The lesion involves the leg; the photograph is a close-up of the affected area; the patient is a male aged 60–69: 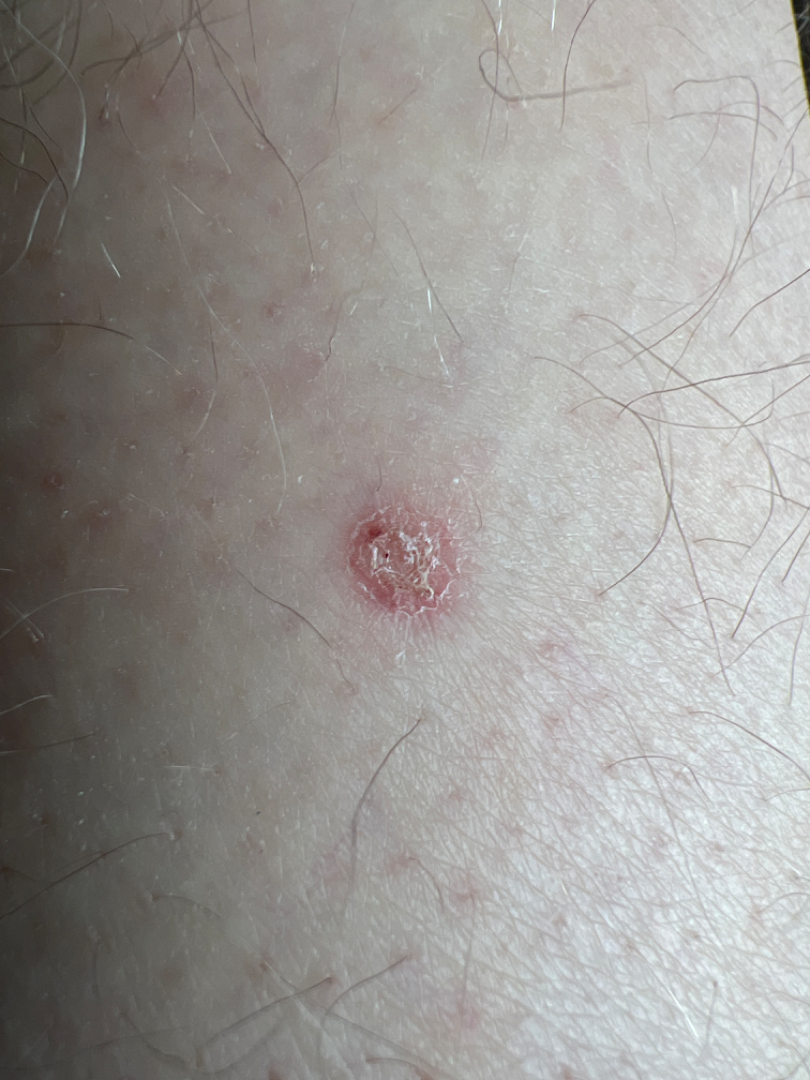The patient indicates itching.
Self-categorized by the patient as a rash.
No constitutional symptoms were reported.
The condition has been present for one to three months.
On independent review by the dermatologists: Basal Cell Carcinoma, SCC/SCCIS, Skin cancer, Psoriasis and Inflicted skin lesions were each considered, in no particular order; a remote consideration is Eczema.